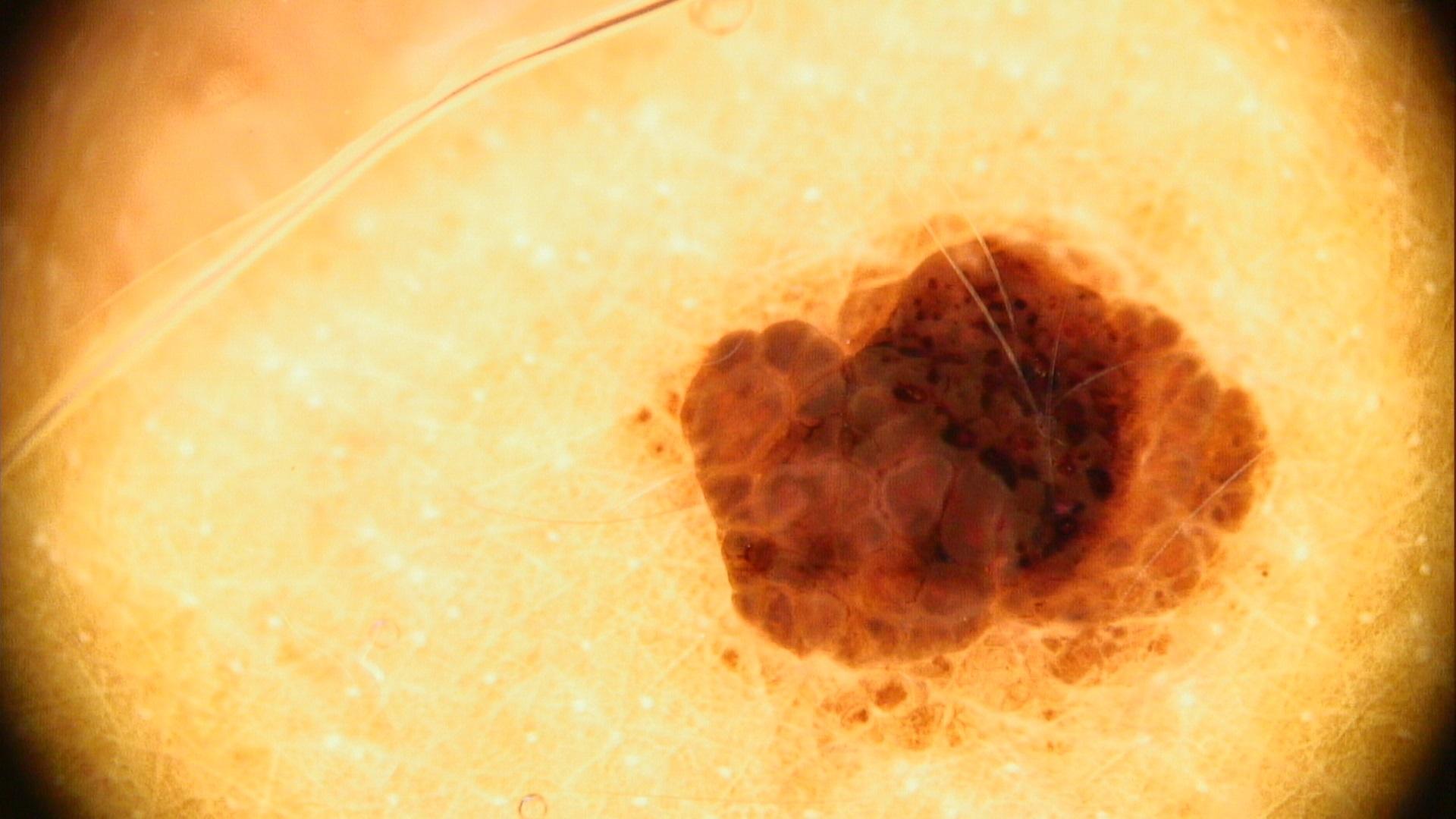Q: What are the patient's age and sex?
A: female, roughly 30 years of age
Q: What is the imaging modality?
A: contact-polarized dermoscopy
Q: Where on the body is the lesion?
A: the trunk
Q: What is this lesion?
A: Nevus (biopsy-proven)